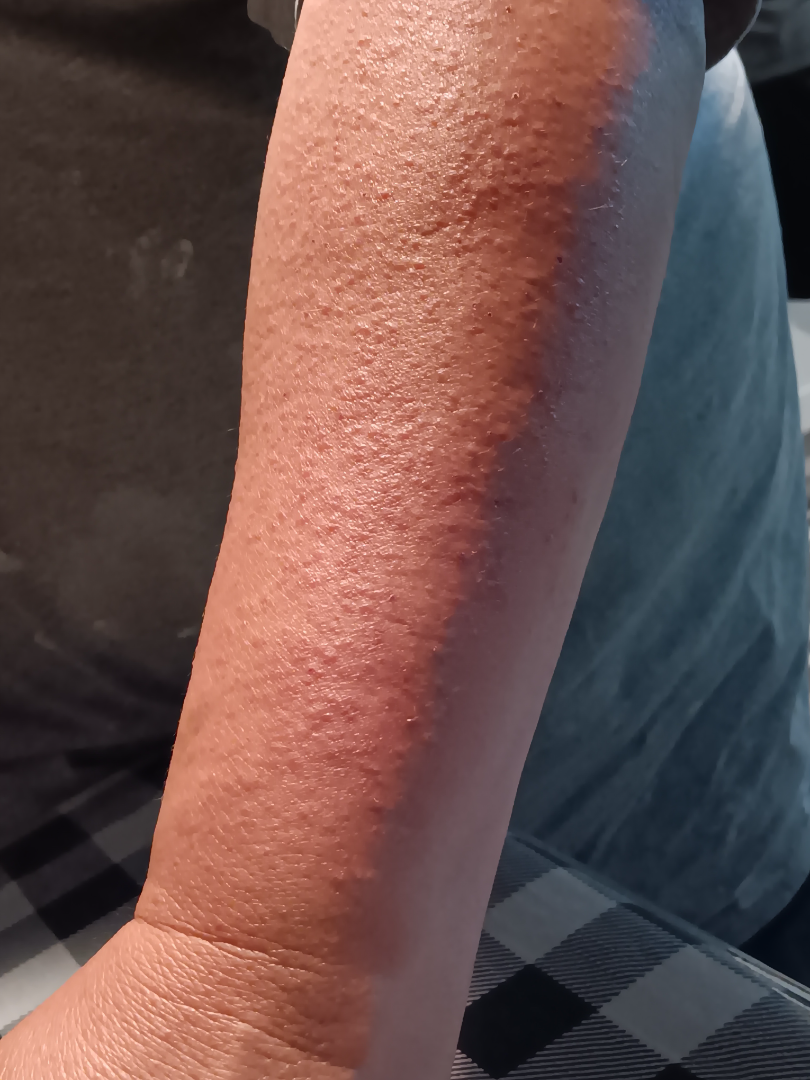The dermatologist could not determine a likely condition from the photograph alone. The photograph was taken at an angle. The affected area is the arm.